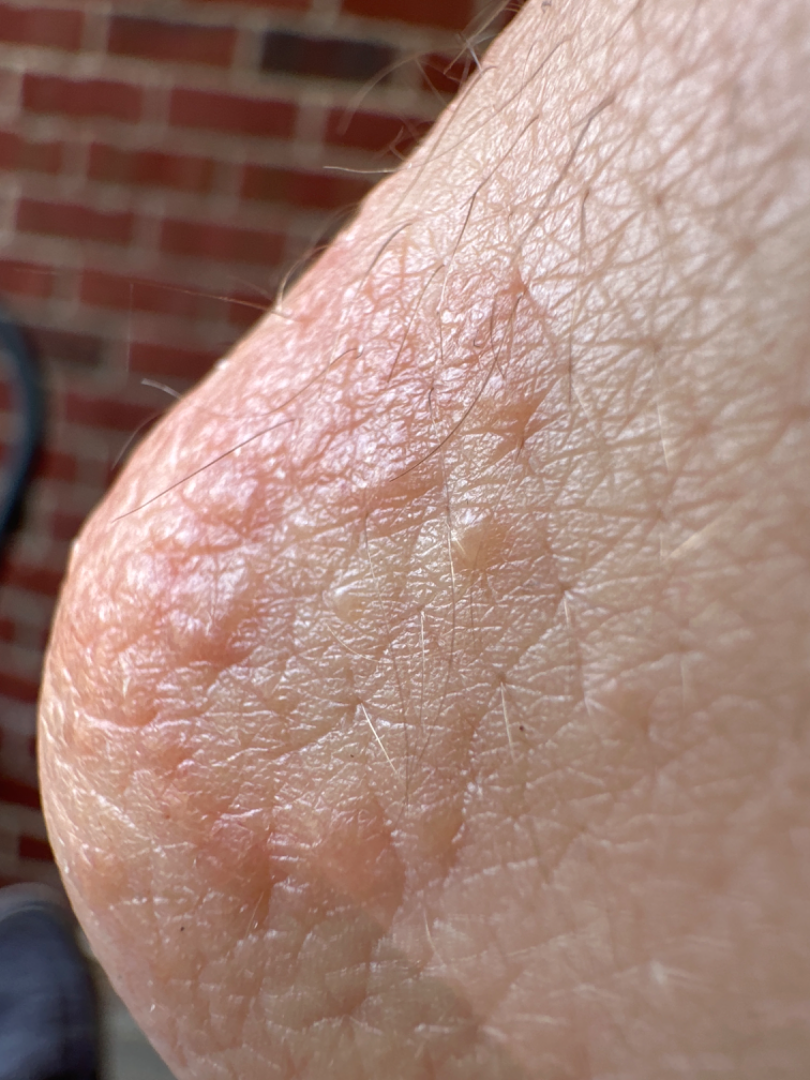Impression:
The case was indeterminate on photographic review.